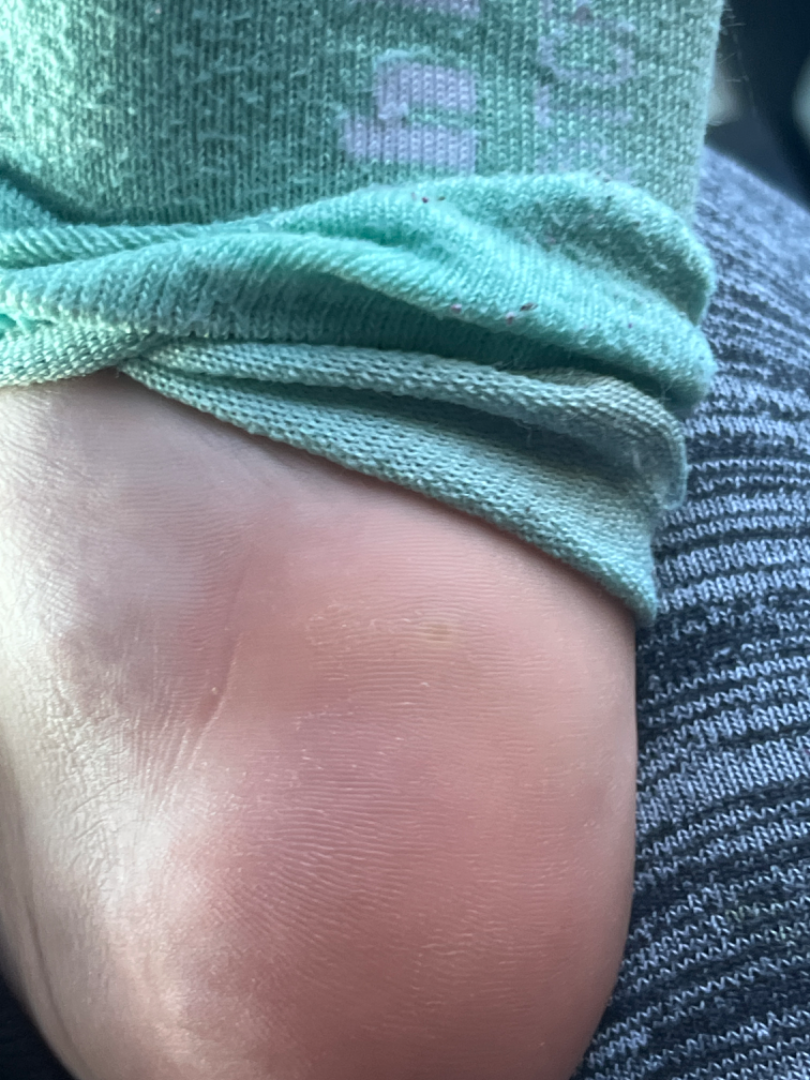{"differential": {"leading": ["Verruca vulgaris"]}}